A clinical photo of a skin lesion taken with a smartphone. The chart records pesticide exposure, tobacco use, alcohol use, prior malignancy (patient or family), and prior skin cancer (patient or family). The patient was assessed as skin type III.
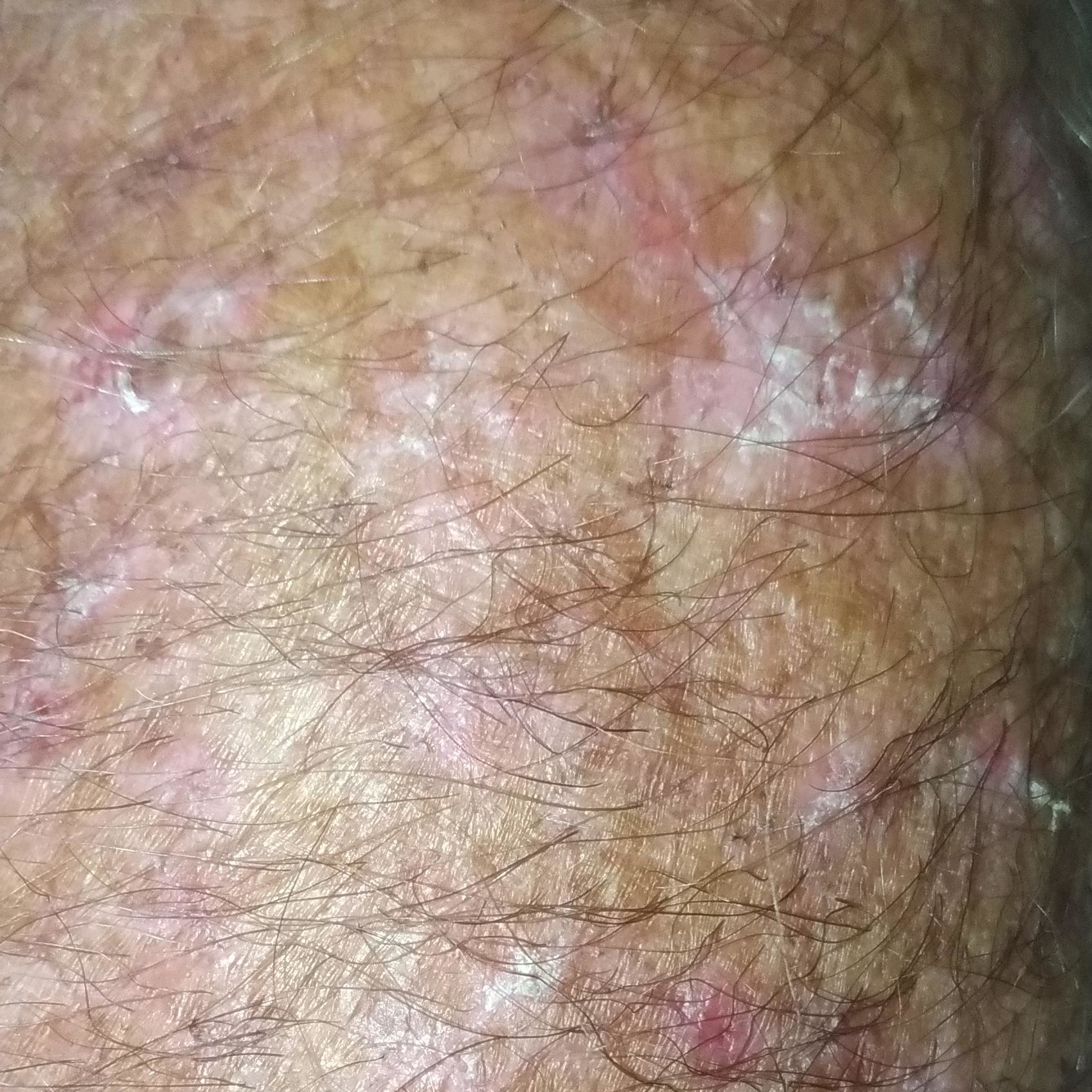– site · a forearm
– lesion diameter · 11 × 8 mm
– reported symptoms · bleeding, itching
– diagnosis · actinic keratosis (clinical consensus)